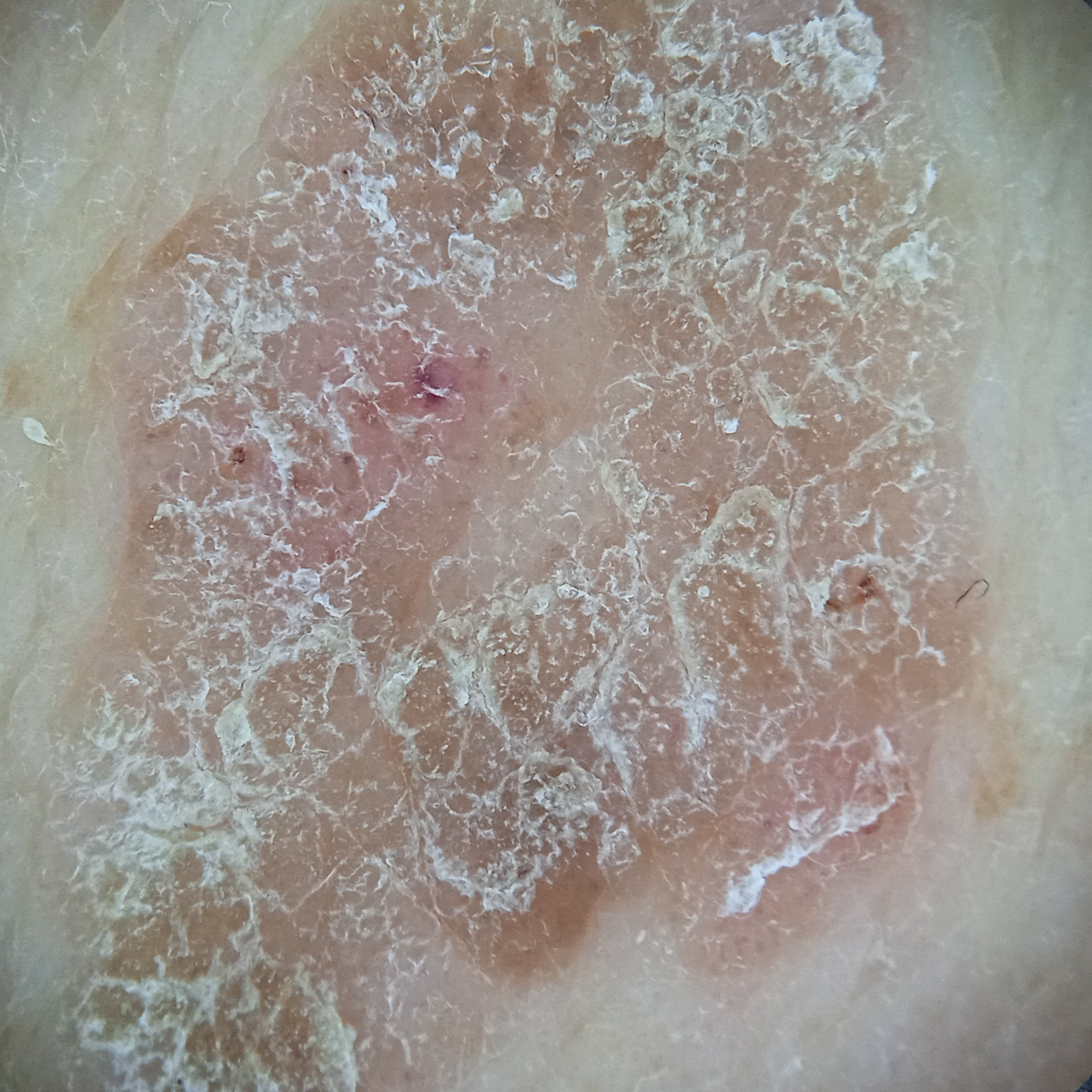sun reaction: skin reddens with sun exposure
referral: research study (no referral diagnosis)
subject: male, aged 72
anatomic site: the back
size: 16.5 mm
assessment: seborrheic keratosis (dermatologist consensus)